A female patient roughly 40 years of age. A dermoscopic image of a skin lesion — 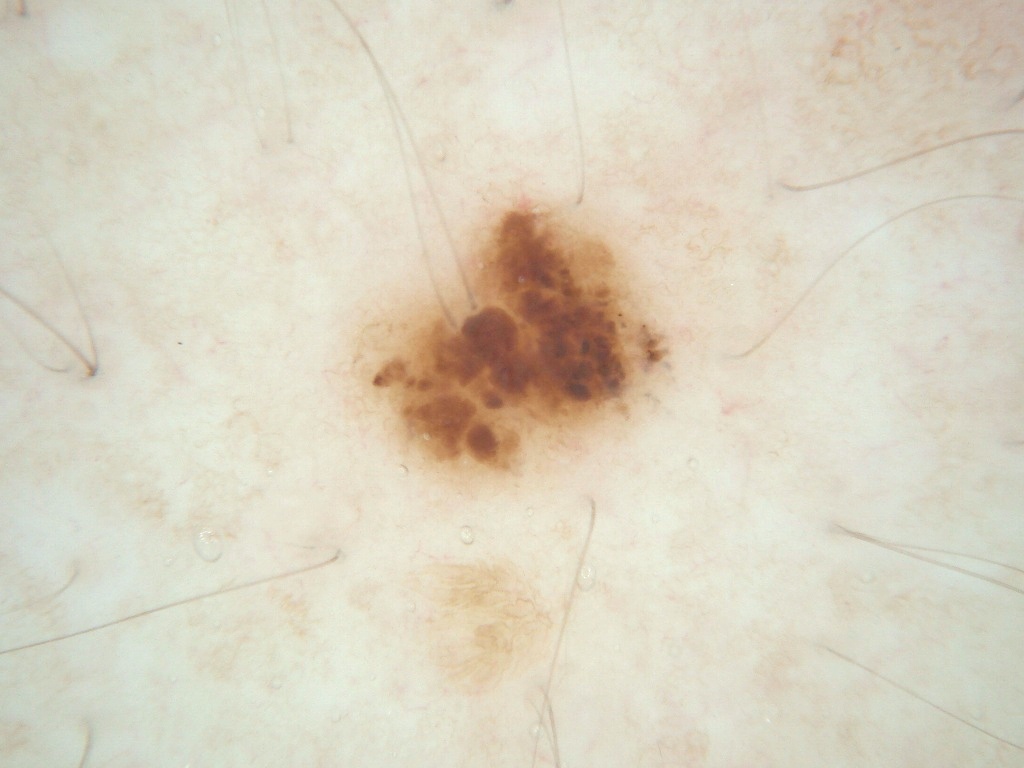Image and clinical context: In (x1, y1, x2, y2) order, the lesion occupies the region [348,192,682,492]. The lesion takes up about 9% of the image. The dermoscopic pattern shows globules; no streaks, negative network, milia-like cysts, or pigment network. Conclusion: The lesion was assessed as a melanocytic nevus.